A male patient 50 years of age. FST II. A smartphone photograph of a skin lesion.
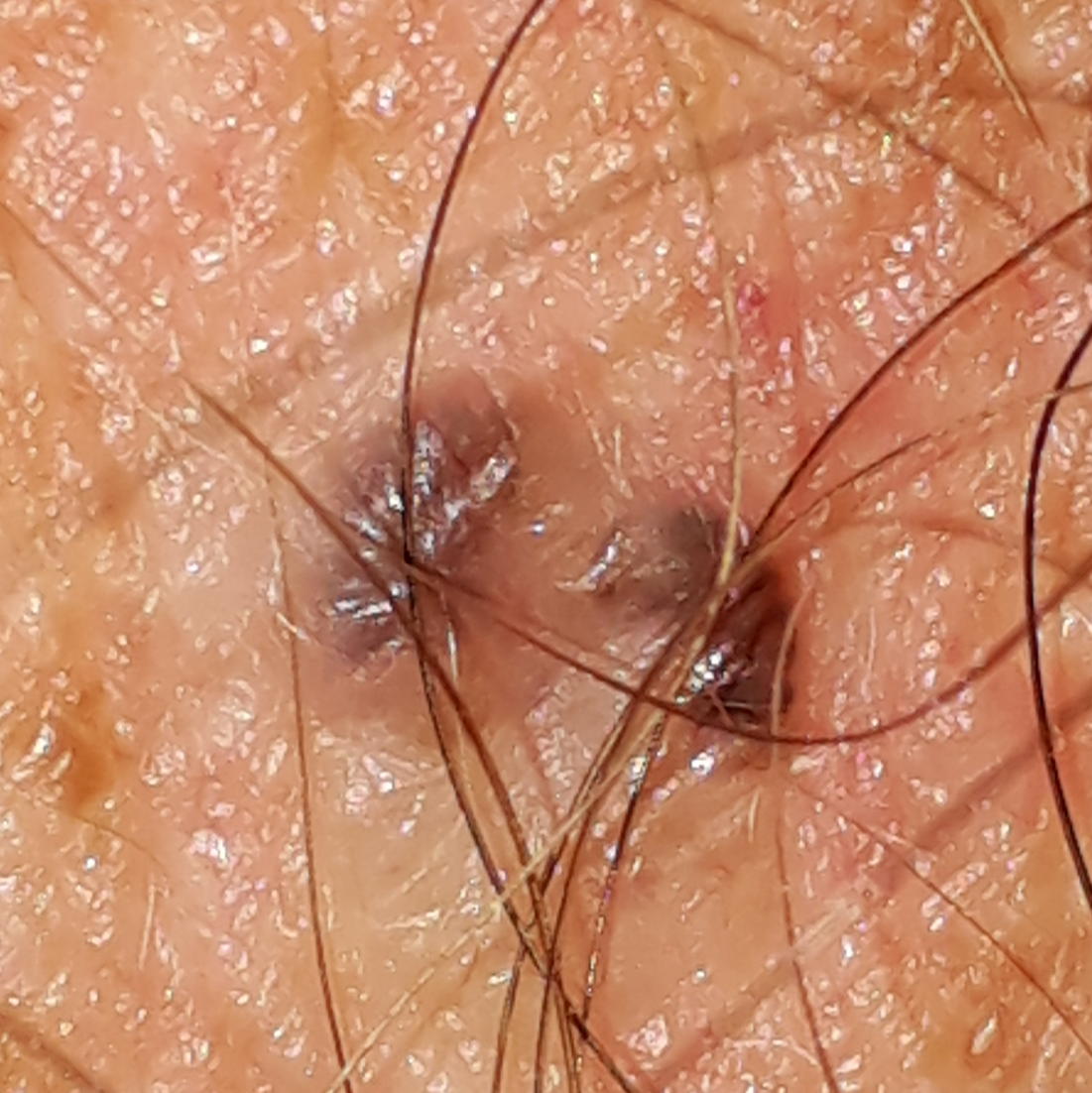Clinical context: The lesion is on the chest. Measuring about 6 × 6 mm. The patient describes that the lesion is elevated and has grown, but has not bled. Diagnosis: Histopathology confirmed a basal cell carcinoma.